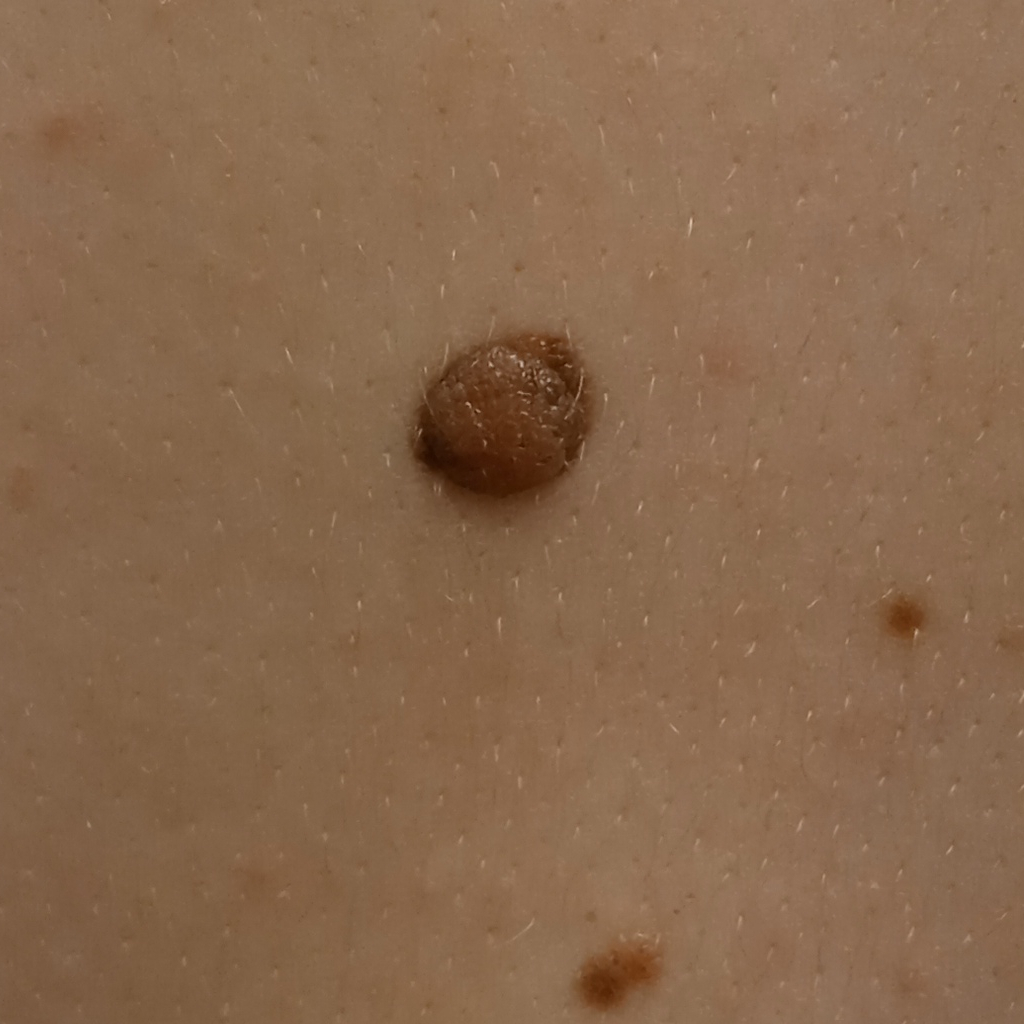Summary:
The patient describes having numerous moles. A clinical photograph of a skin lesion. Collected as part of a research study, without a referral diagnosis. The patient reports a history of sunbed use. A female subject 26 years of age. The patient says their skin reddens with sun exposure. The lesion involves the back. The lesion is about 8.9 mm across.
Conclusion:
The dermatologists' assessment was a melanocytic nevus.